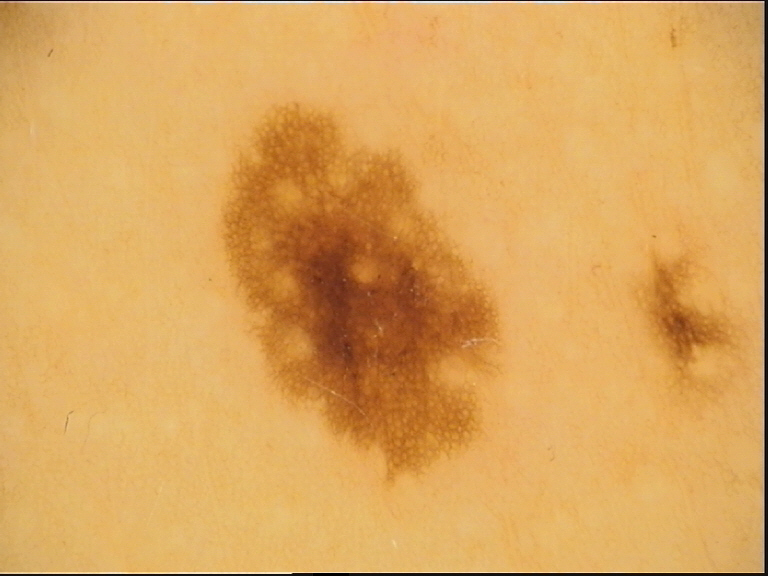A dermoscopic photograph of a skin lesion.
Consistent with a benign lesion — a dysplastic junctional nevus.